A dermoscopic close-up of a skin lesion.
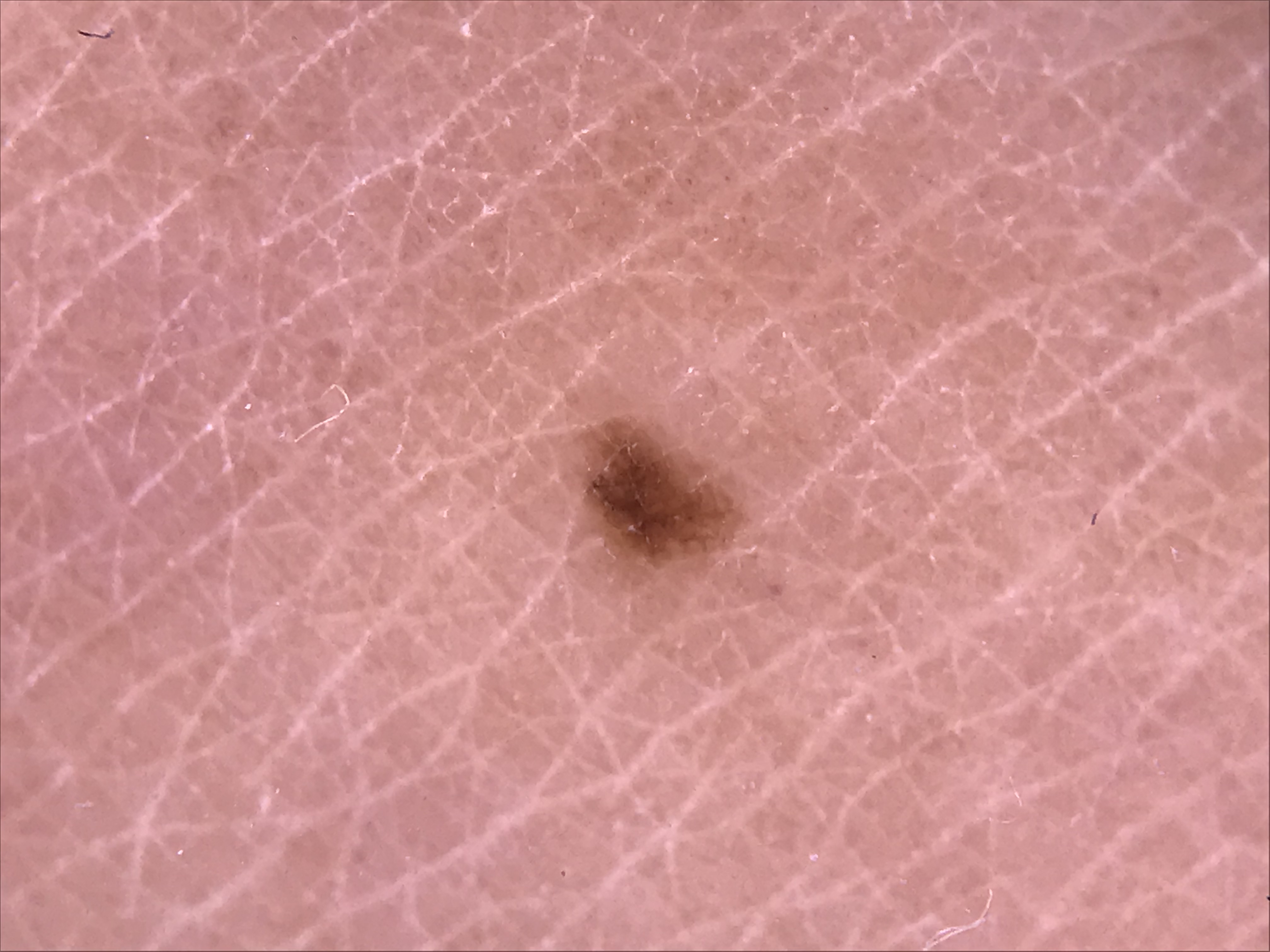Diagnosed as a banal lesion — a junctional nevus.